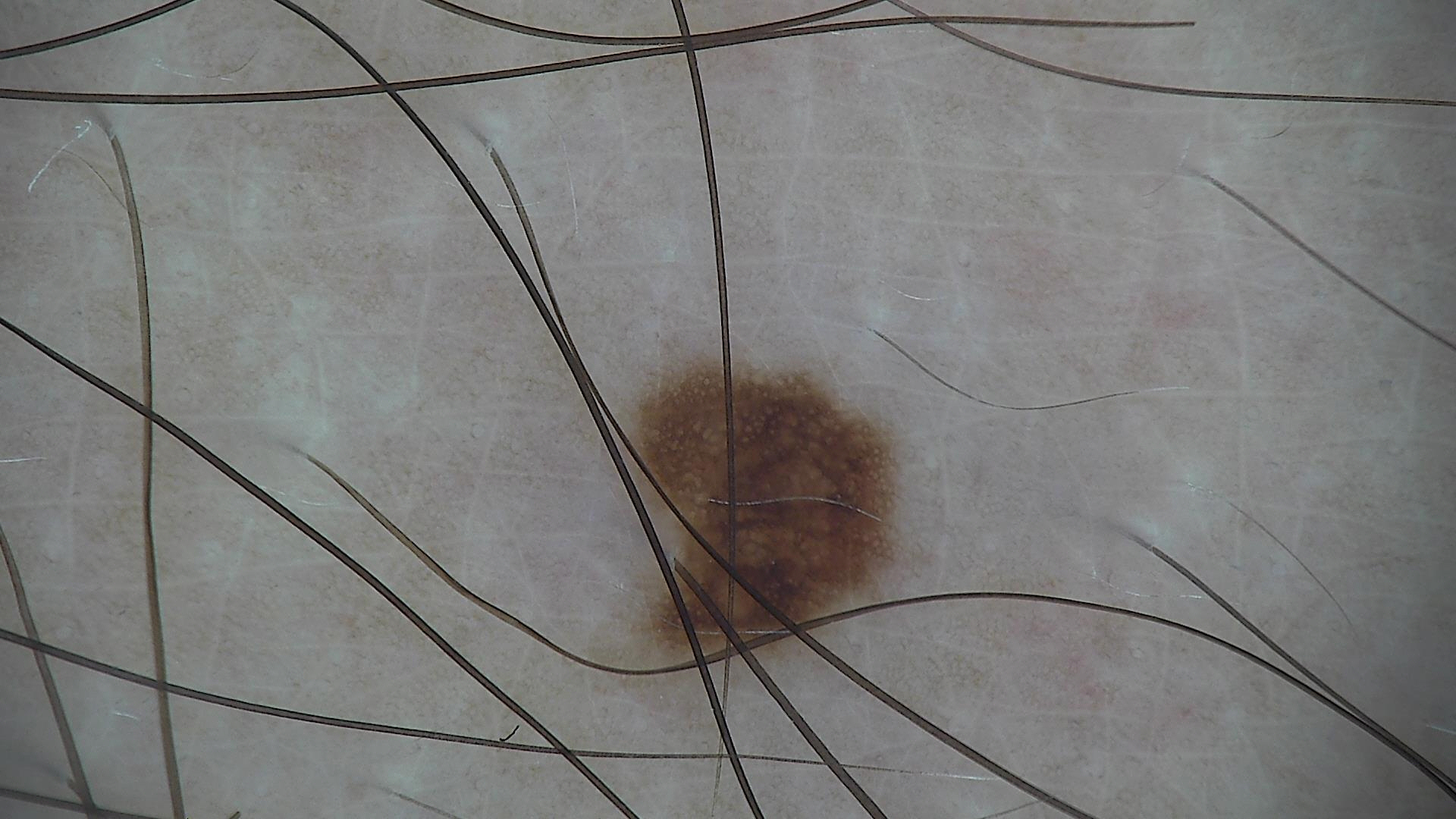Findings:
A dermoscopic photograph of a skin lesion.
Conclusion:
Consistent with a benign lesion — a dysplastic junctional nevus.